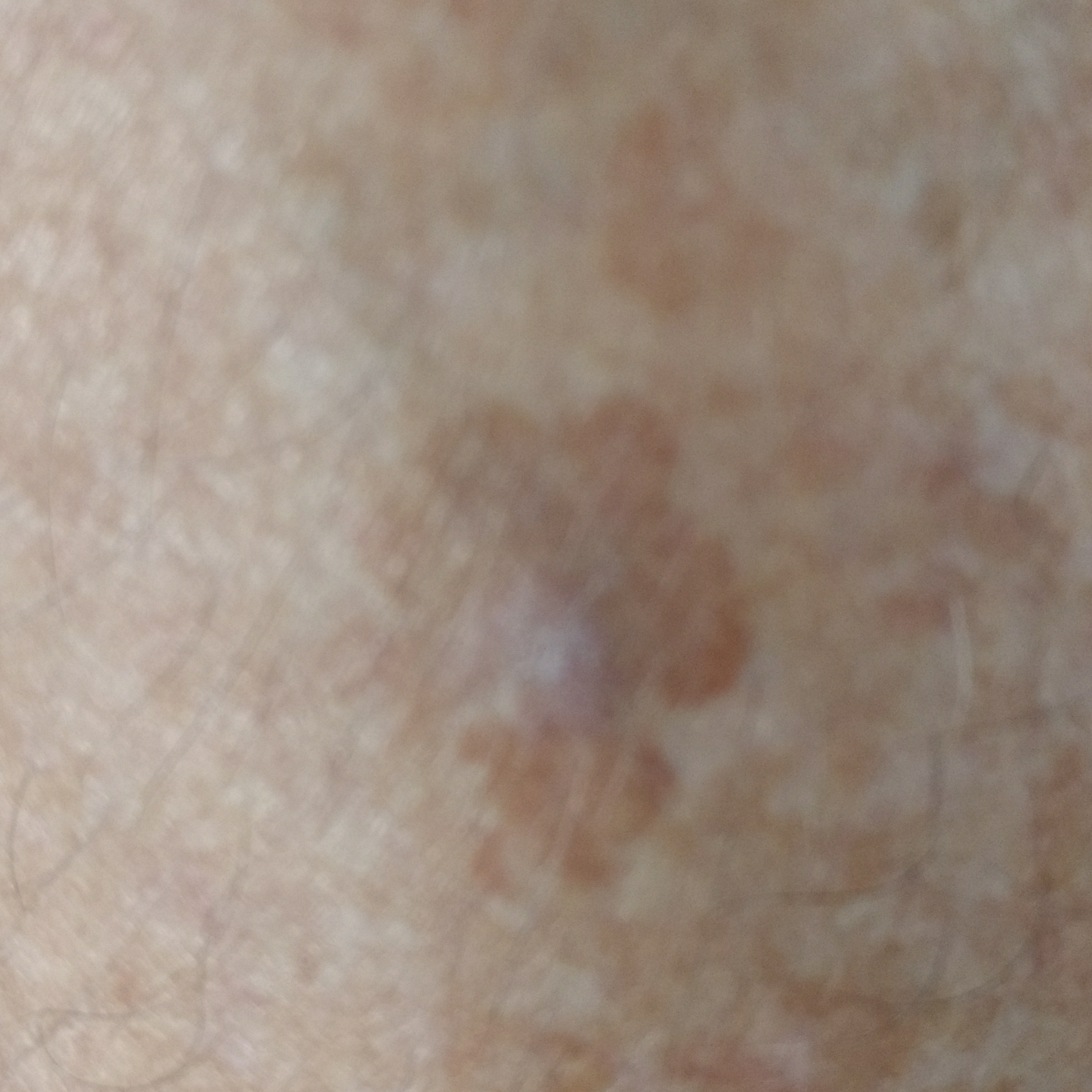Q: What was the clinical impression?
A: seborrheic keratosis (clinical consensus)